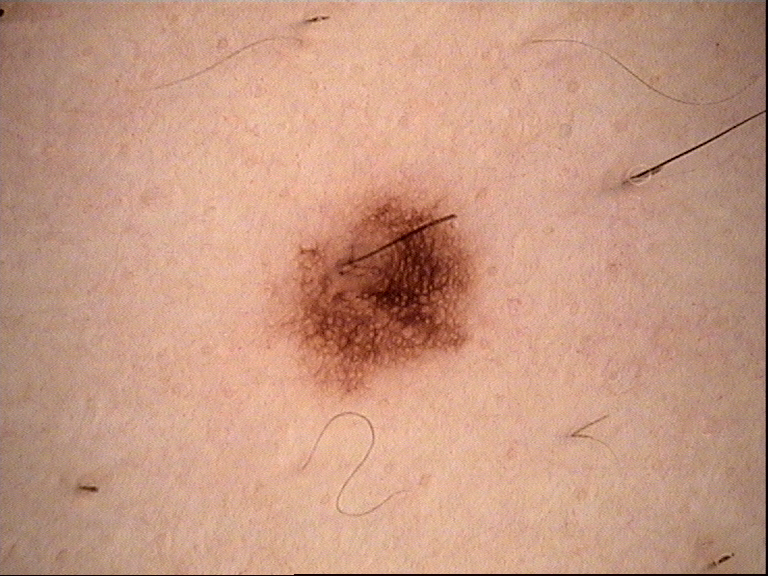imaging = dermoscopy; class = dysplastic junctional nevus (expert consensus).